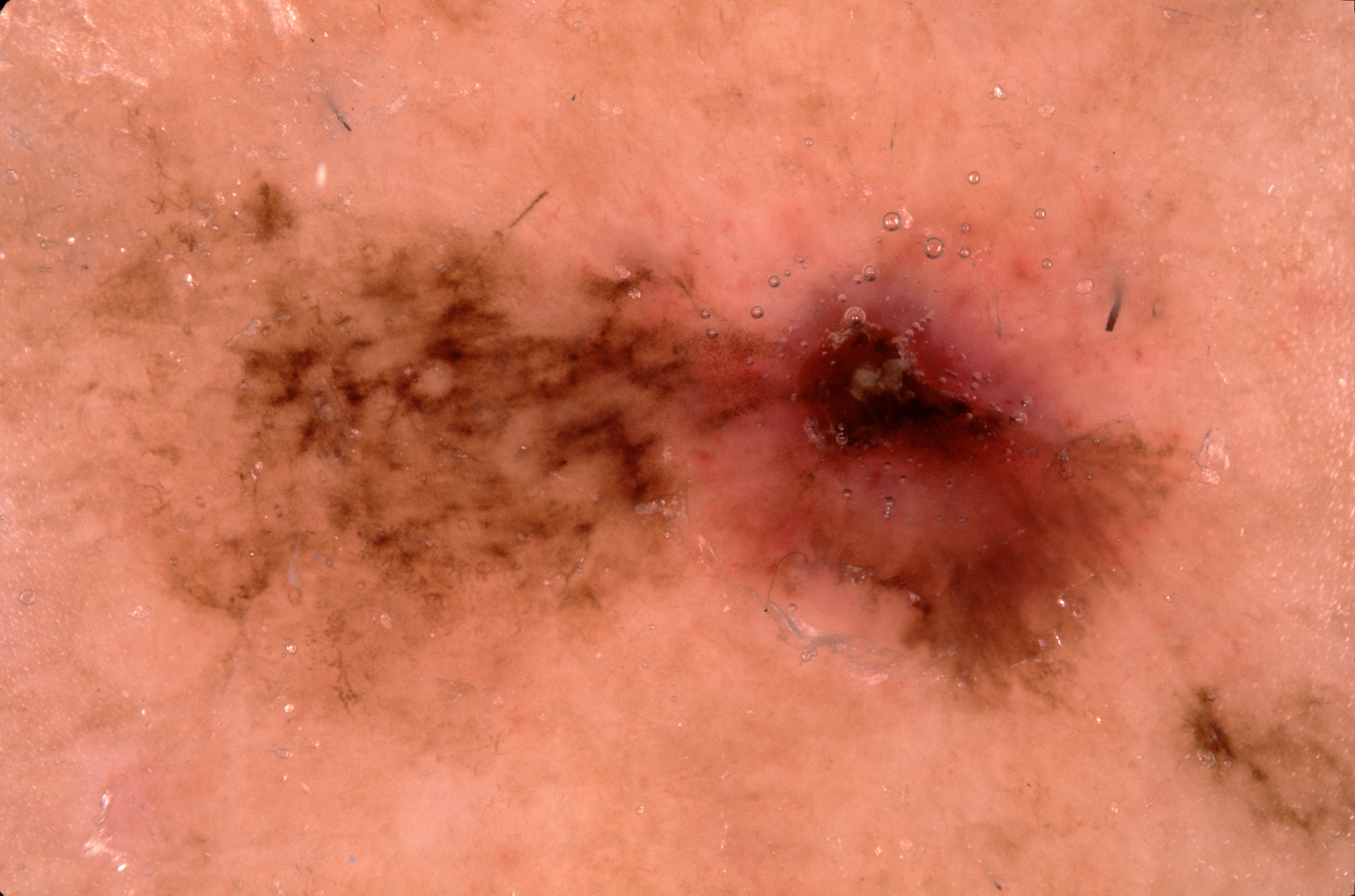imaging = dermoscopy
location = x1=0, y1=102, x2=1354, y2=881
diagnosis = a melanoma